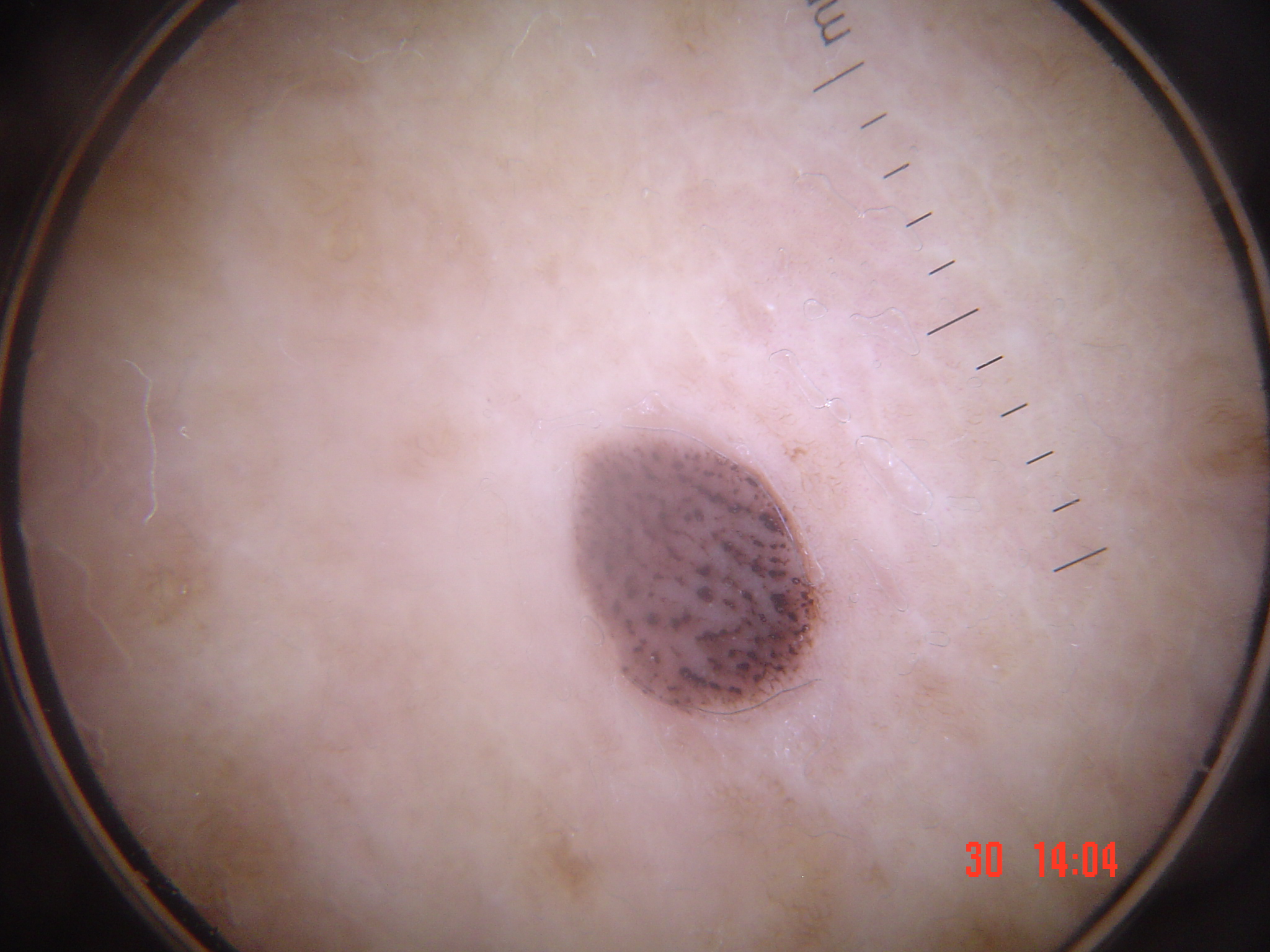image type = dermoscopy; diagnostic label = seborrheic keratosis (expert consensus).